A dermoscopic photograph of a skin lesion: 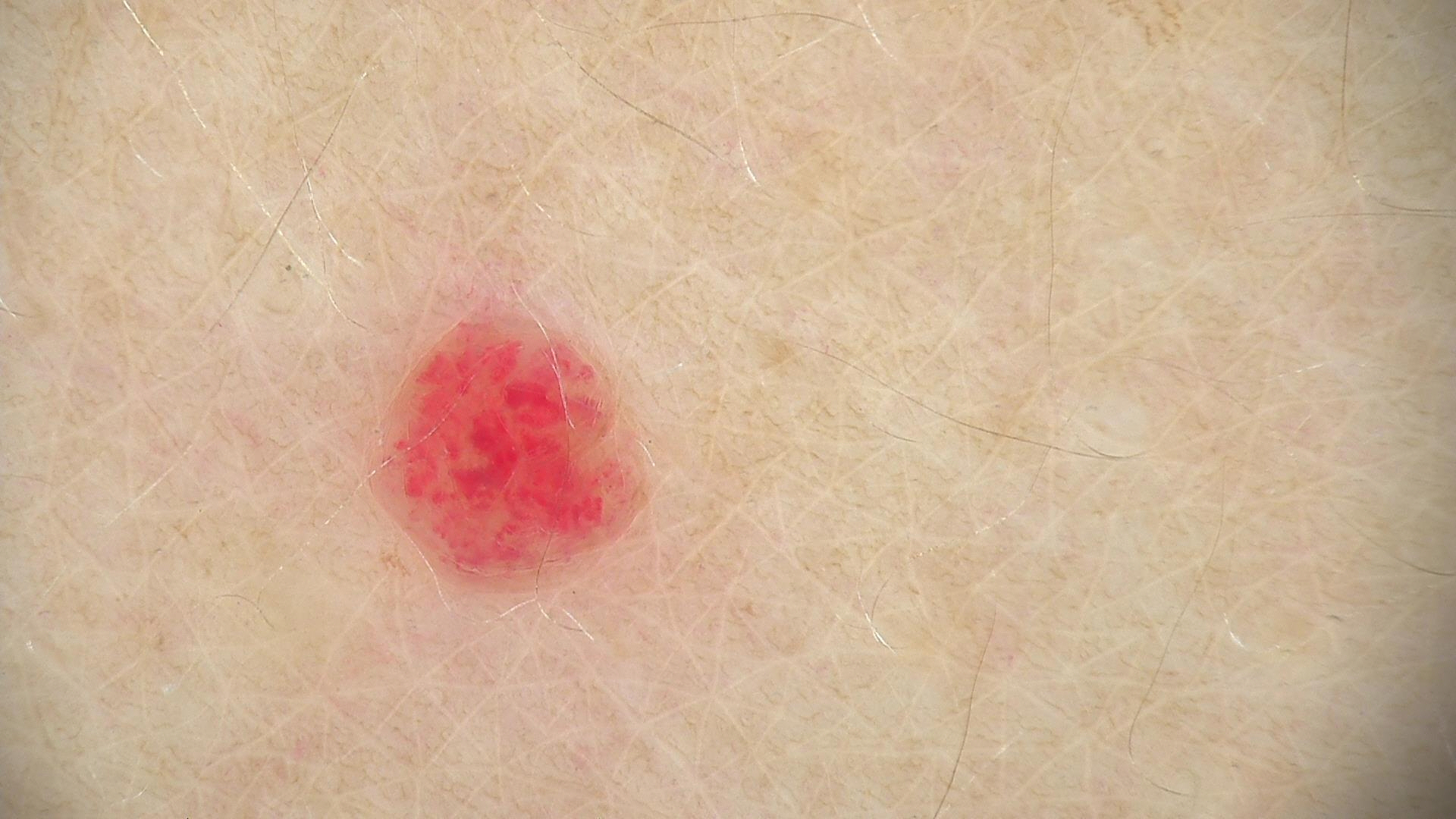<dermoscopy>
<lesion_type>
<main_class>vascular</main_class>
</lesion_type>
<diagnosis>
<name>hemangioma</name>
<code>ha</code>
<malignancy>benign</malignancy>
<super_class>non-melanocytic</super_class>
<confirmation>expert consensus</confirmation>
</diagnosis>
</dermoscopy>